The patient is a female aged 40–49; the photograph was taken at an angle; the lesion involves the arm.
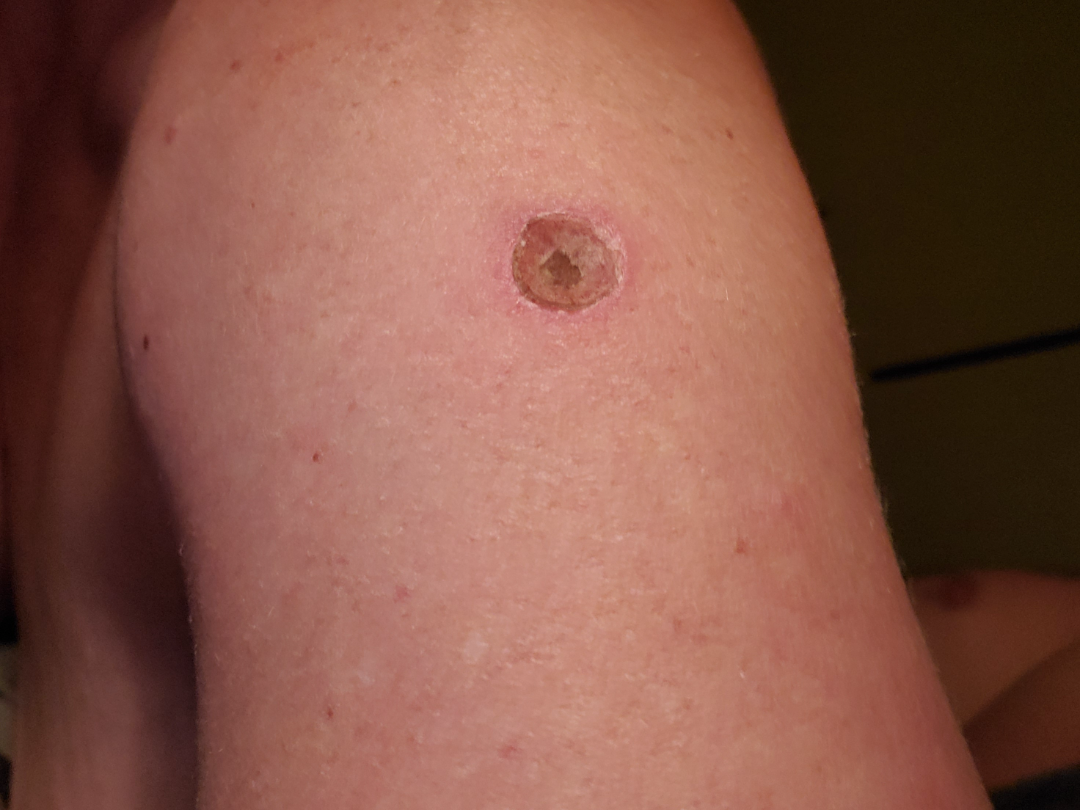The patient reports the condition has been present for less than one week. The patient reported no relevant symptoms from the lesion. The favored diagnosis is Ecthyma; the differential also includes Chronic ulcer of skin; also consider Skin lesion in drug addict.